The contributor notes the condition has been present for one to four weeks. No relevant systemic symptoms. The affected area is the arm. The contributor notes the lesion is raised or bumpy. An image taken at an angle. Symptoms reported: itching: 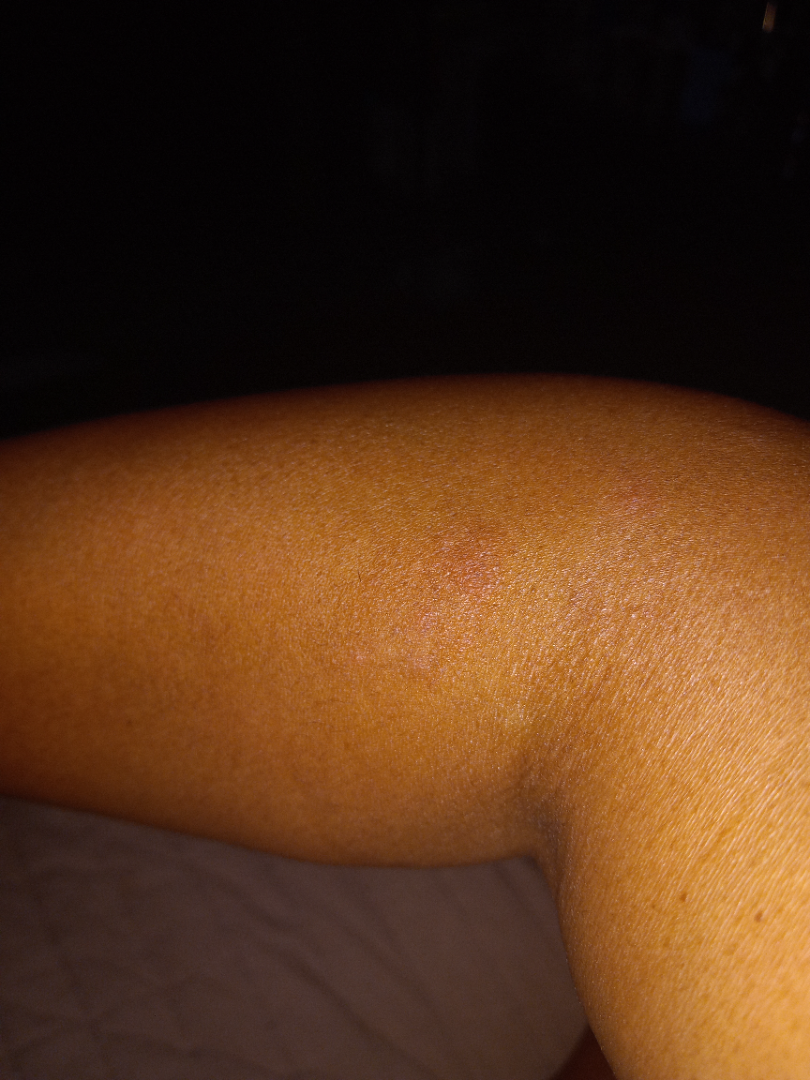differential: Eczema